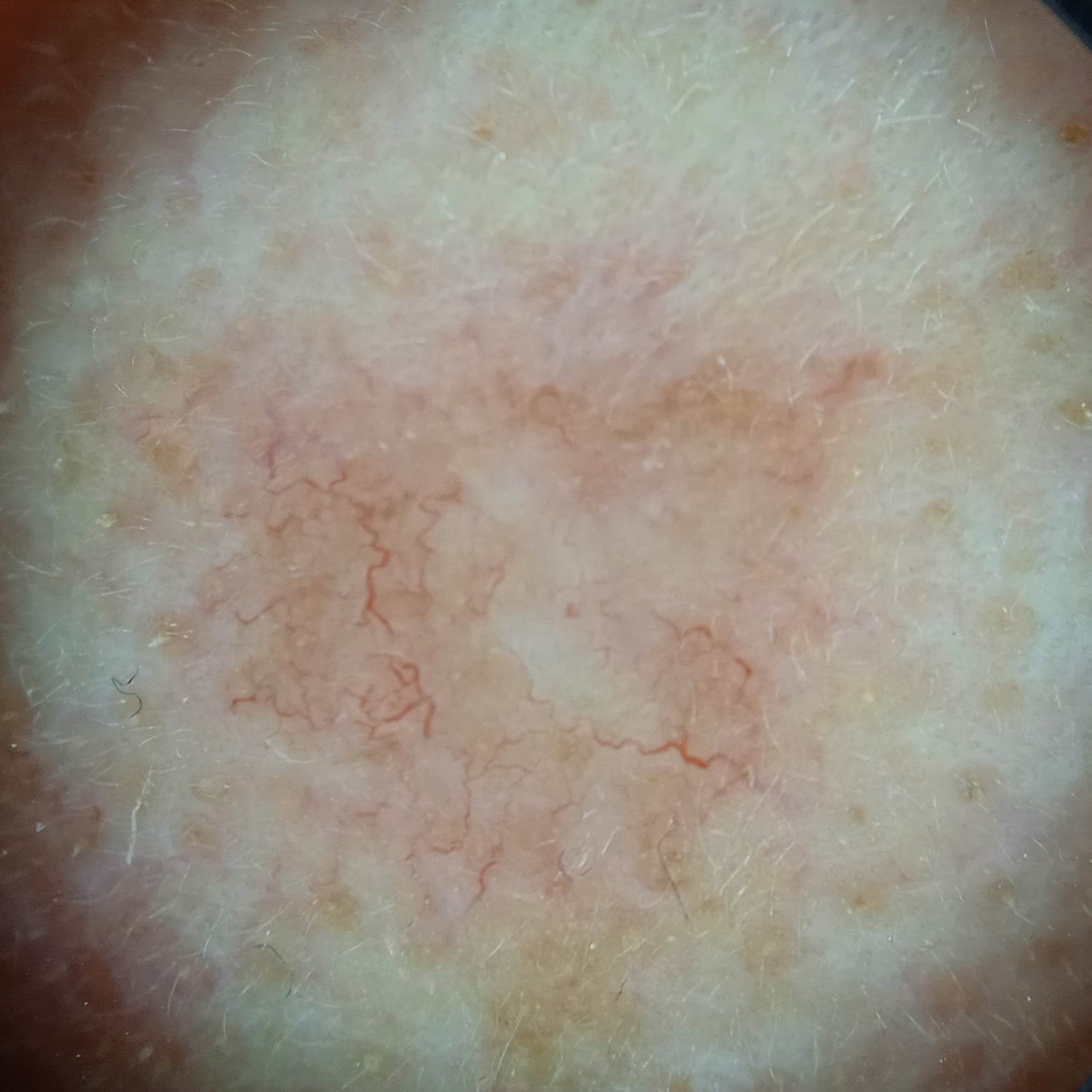{"risk_factors": {"positive": ["a personal history of cancer"], "negative": ["no family history of skin cancer"]}, "patient": {"age": 84, "sex": "female"}, "image": "dermoscopy", "mole_burden": "few melanocytic nevi overall", "referral": "clinical suspicion of basal cell carcinoma", "sun_reaction": "skin tans without first burning", "lesion_location": "the face", "diagnosis": {"name": "basal cell carcinoma", "malignancy": "malignant", "procedure": "excision", "tumor_thickness_mm": 1.5}}